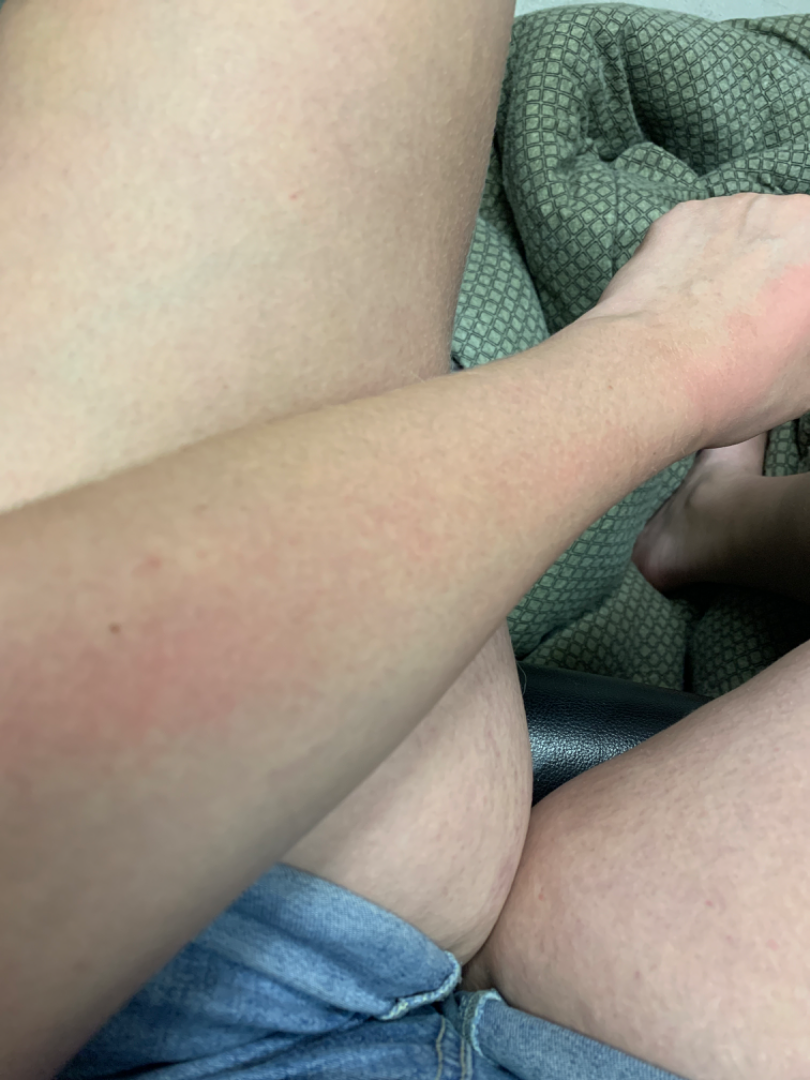{
  "assessment": "unable to determine",
  "body_site": "arm",
  "shot_type": "at an angle"
}